A dermoscopic close-up of a skin lesion.
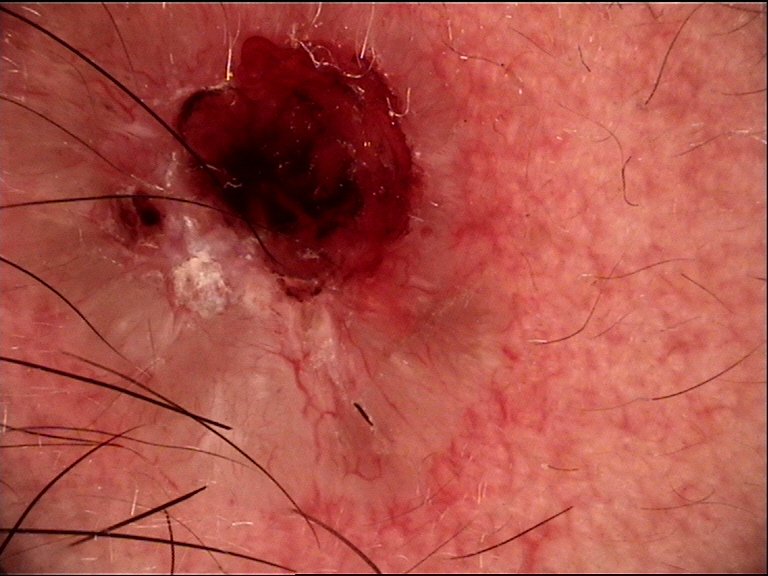This is a keratinocytic lesion.
Biopsy-confirmed as a basal cell carcinoma.